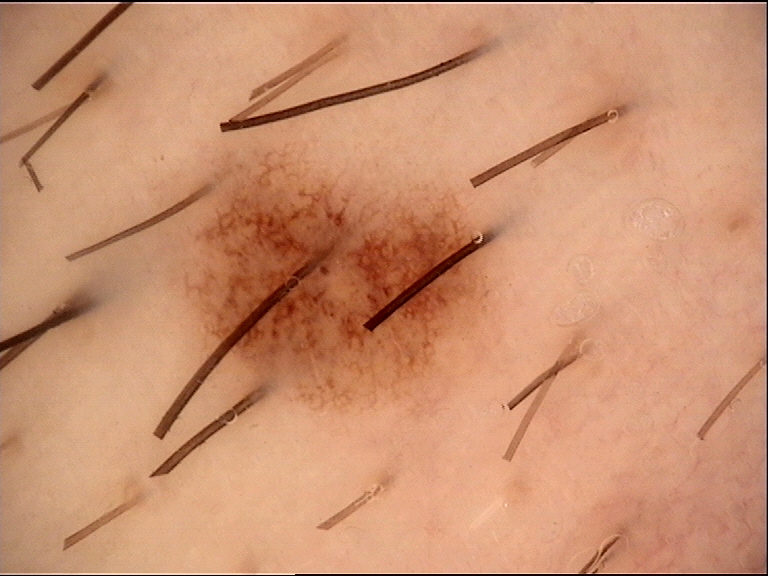class: dysplastic junctional nevus (expert consensus).